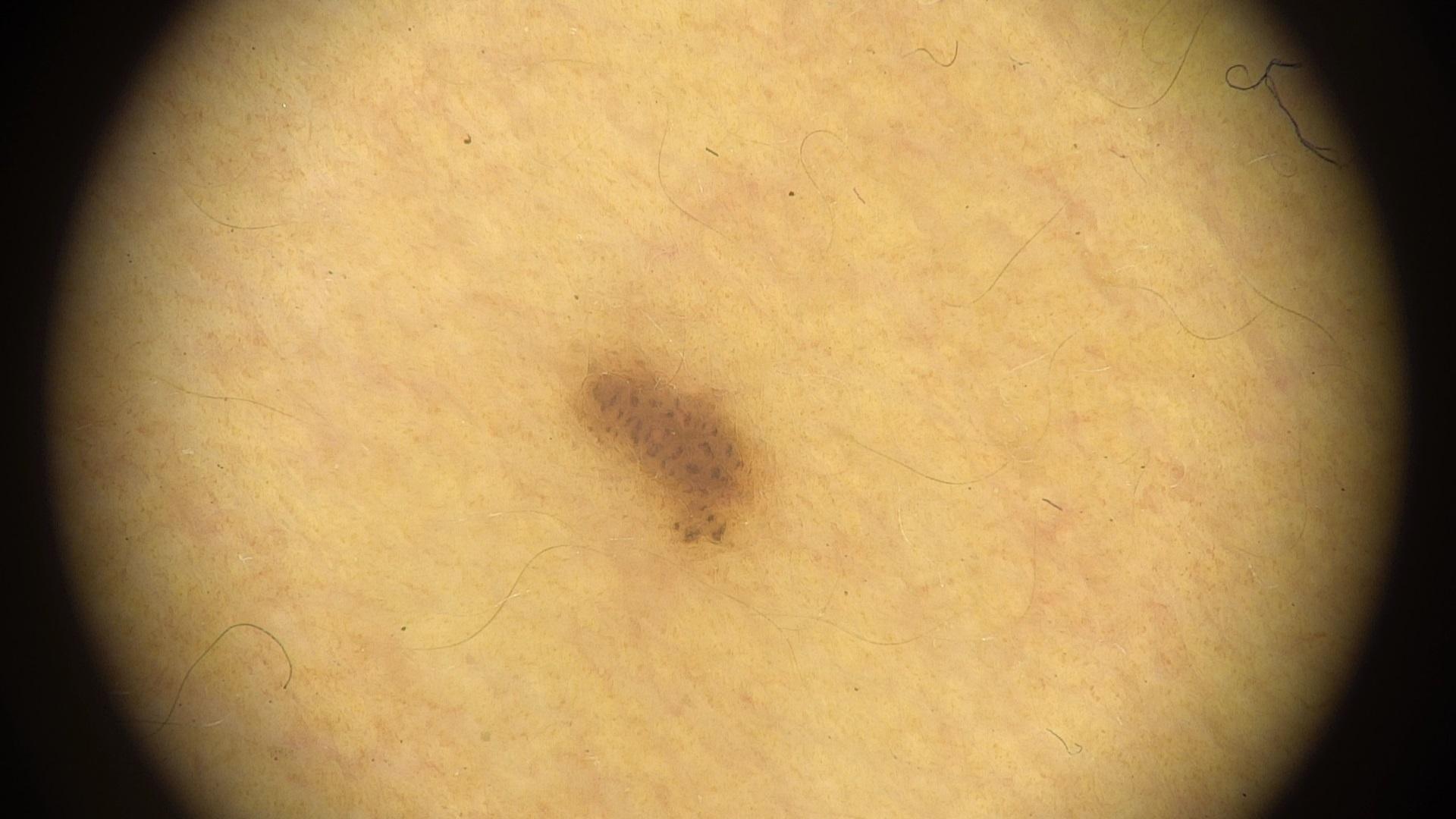Conclusion: Consistent with a nevus.